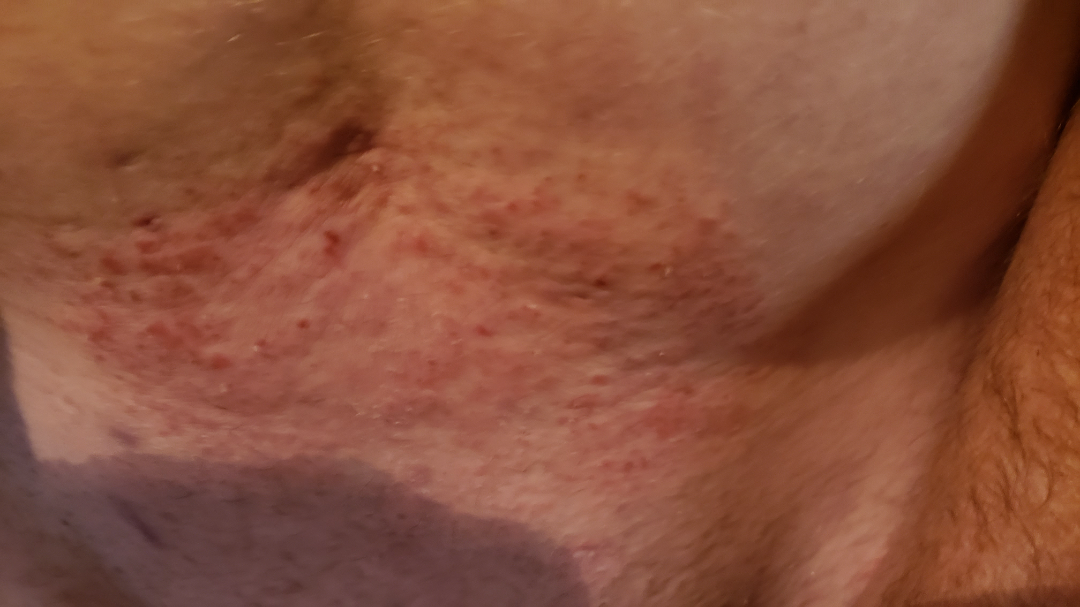Impression:
Single-reviewer assessment: in keeping with Lichenified eczematous dermatitis.